This is a close-up image — 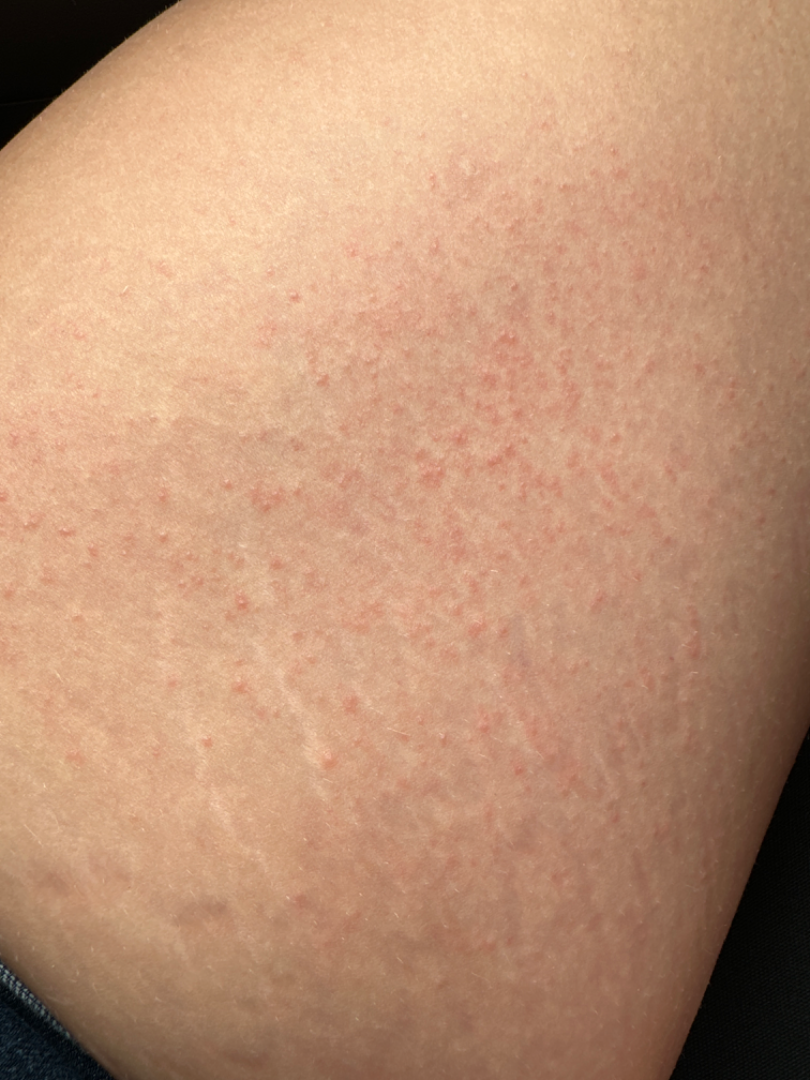| feature | finding |
|---|---|
| assessment | indeterminate from the photograph |